A clinical photo of a skin lesion taken with a smartphone; a female patient in their mid-50s:
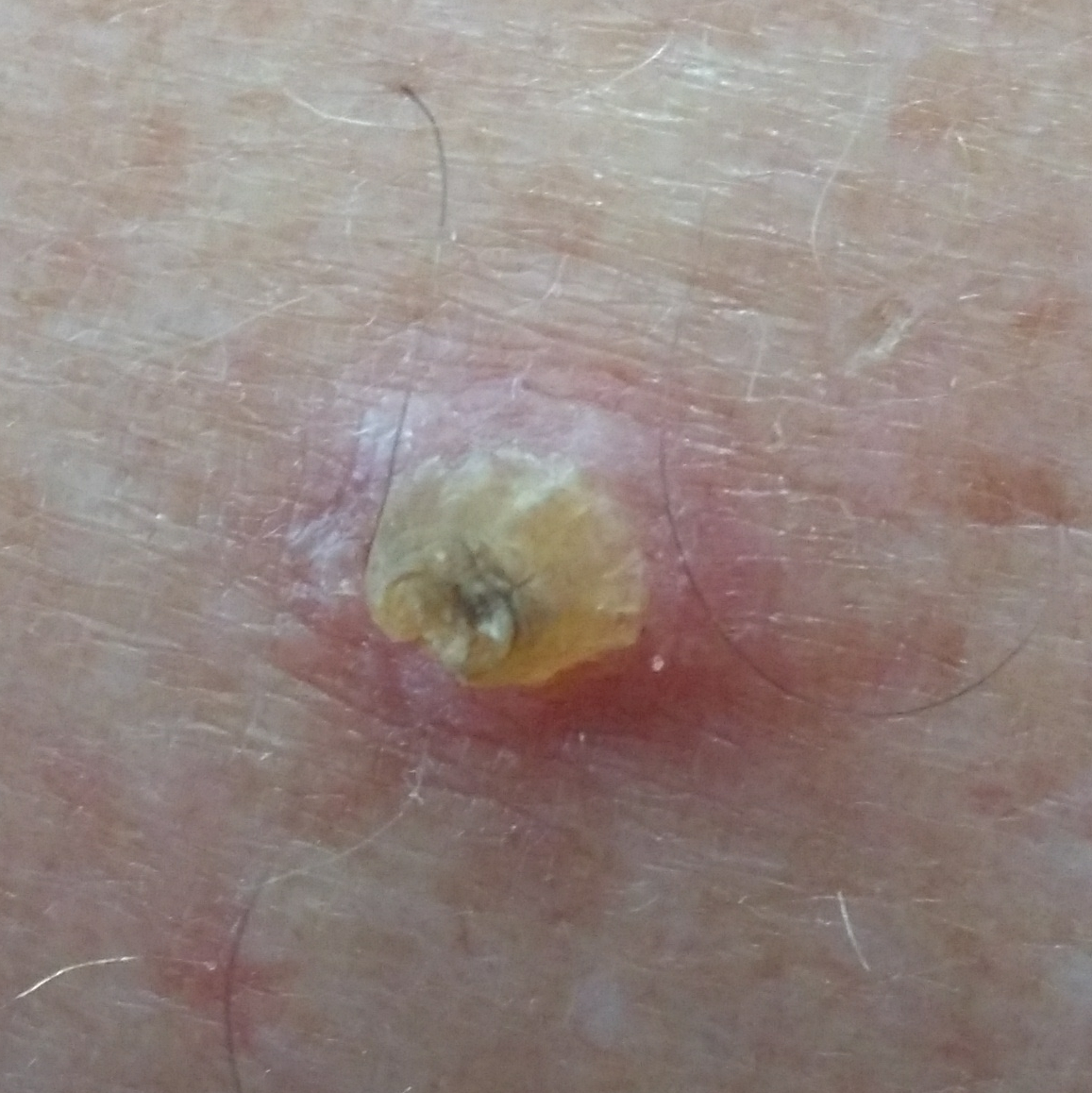{
  "diagnosis": {
    "name": "actinic keratosis",
    "code": "ACK",
    "malignancy": "indeterminate",
    "confirmation": "histopathology"
  }
}